The patient is a male aged 40–49, the lesion involves the head or neck, a close-up photograph:
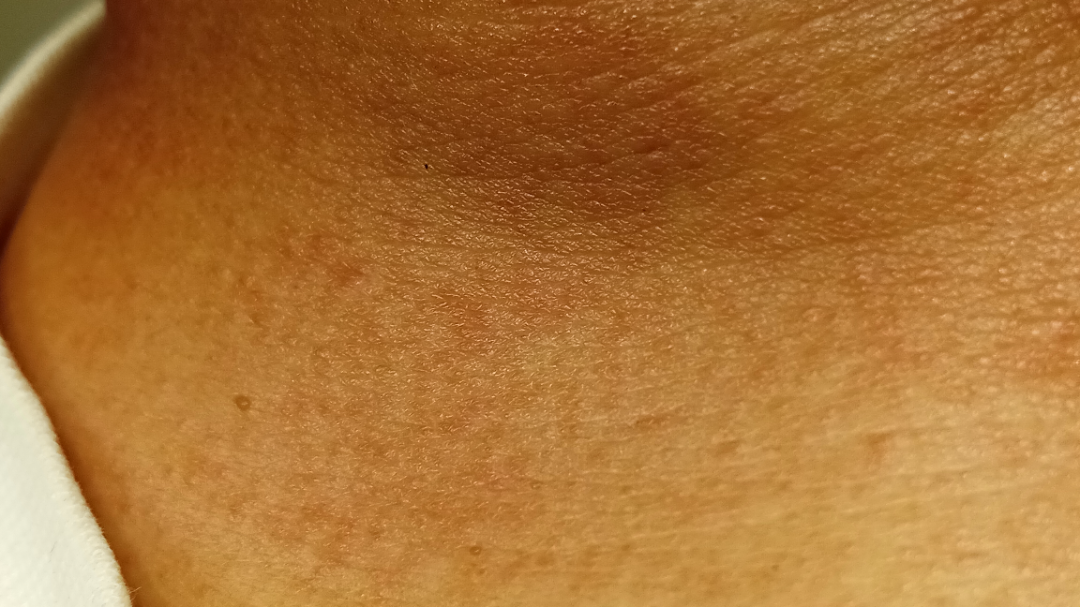assessment = could not be assessed.